The affected area is the leg; an image taken at a distance: 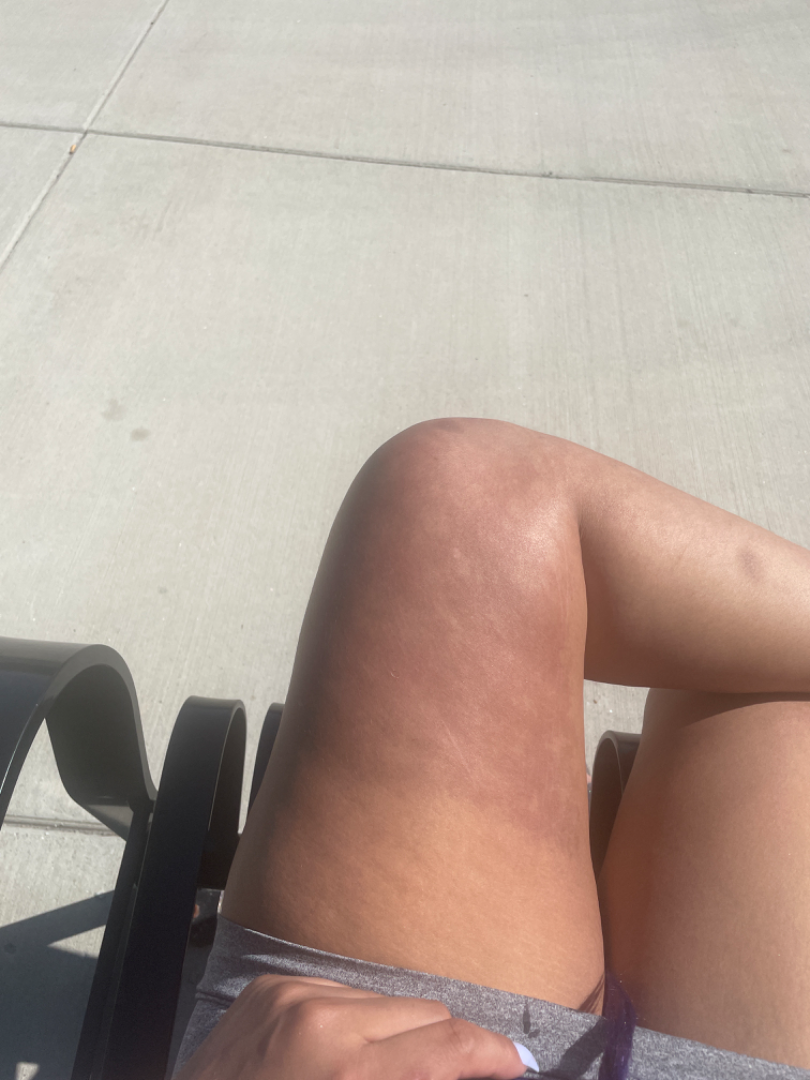Review:
On dermatologist assessment of the image: favoring Post-Inflammatory hyperpigmentation; also raised was Erythema ab igne; less likely is Erythema dyschromicum perstans.